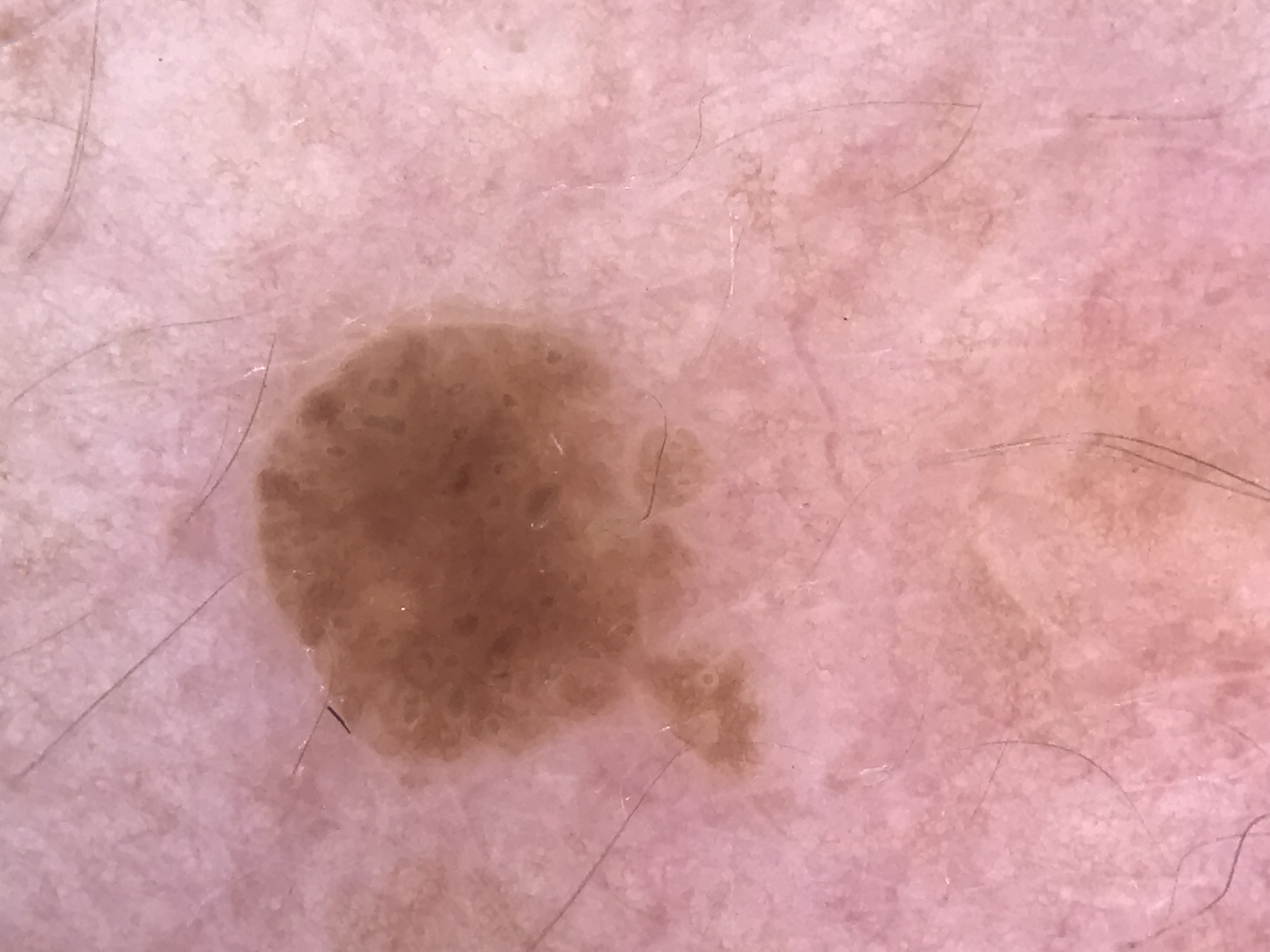modality = dermatoscopy | subtype = keratinocytic | diagnosis = seborrheic keratosis (expert consensus).